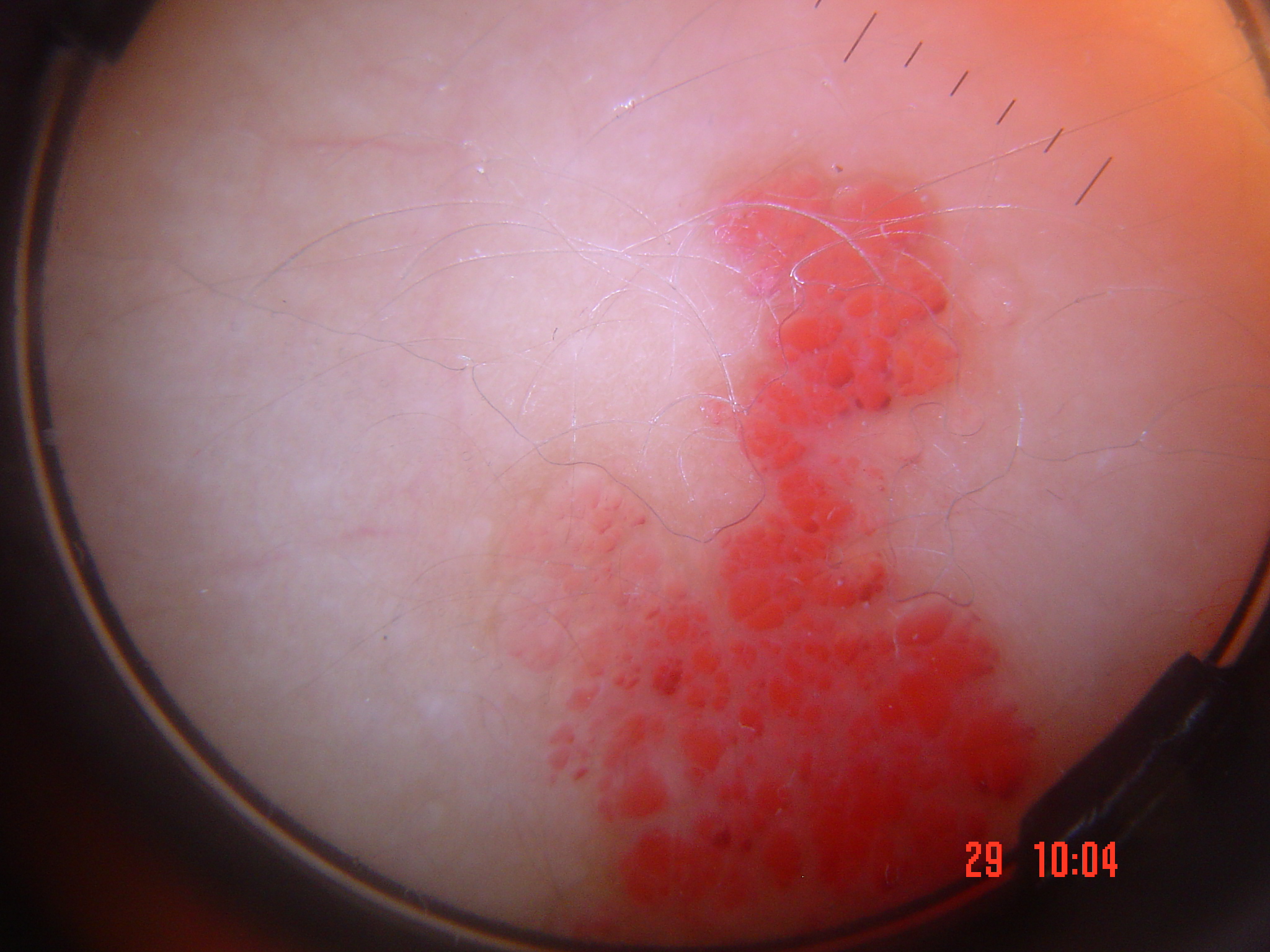Labeled as a lymphangioma.